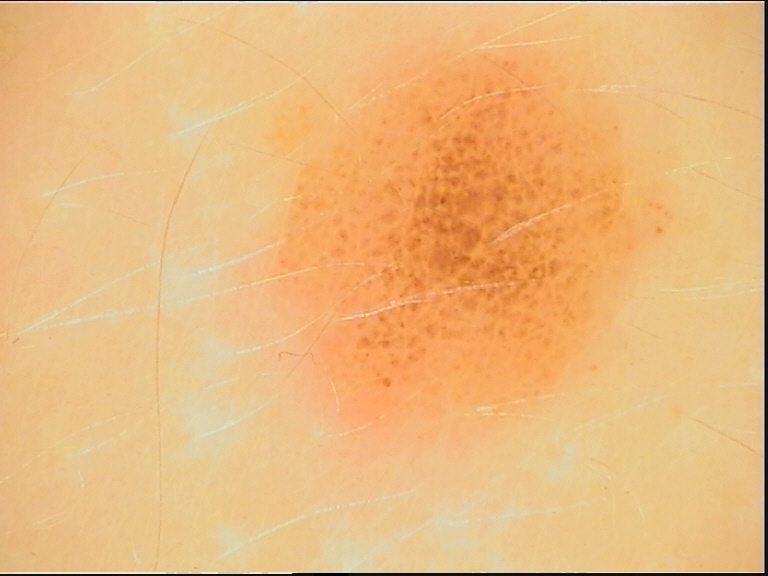Impression:
Diagnosed as a dysplastic compound nevus.